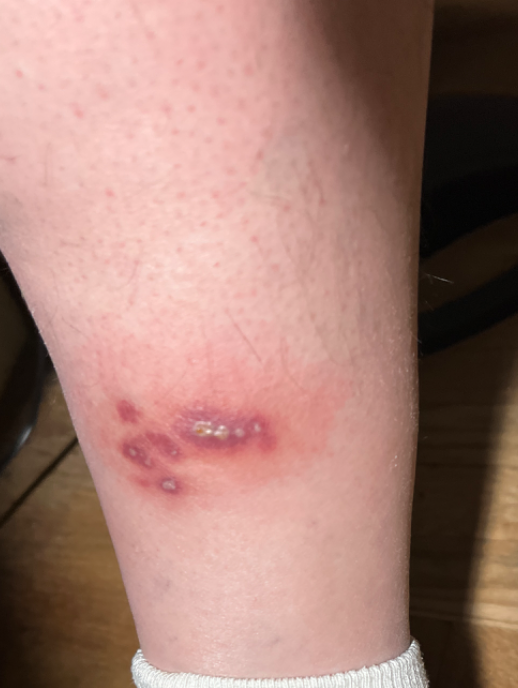Case summary:
– image framing · at an angle
– impression · Insect Bite (primary); Pyoderma Gangrenosum (possible); purulent pustules (possible)